A dermoscopic image of a skin lesion:
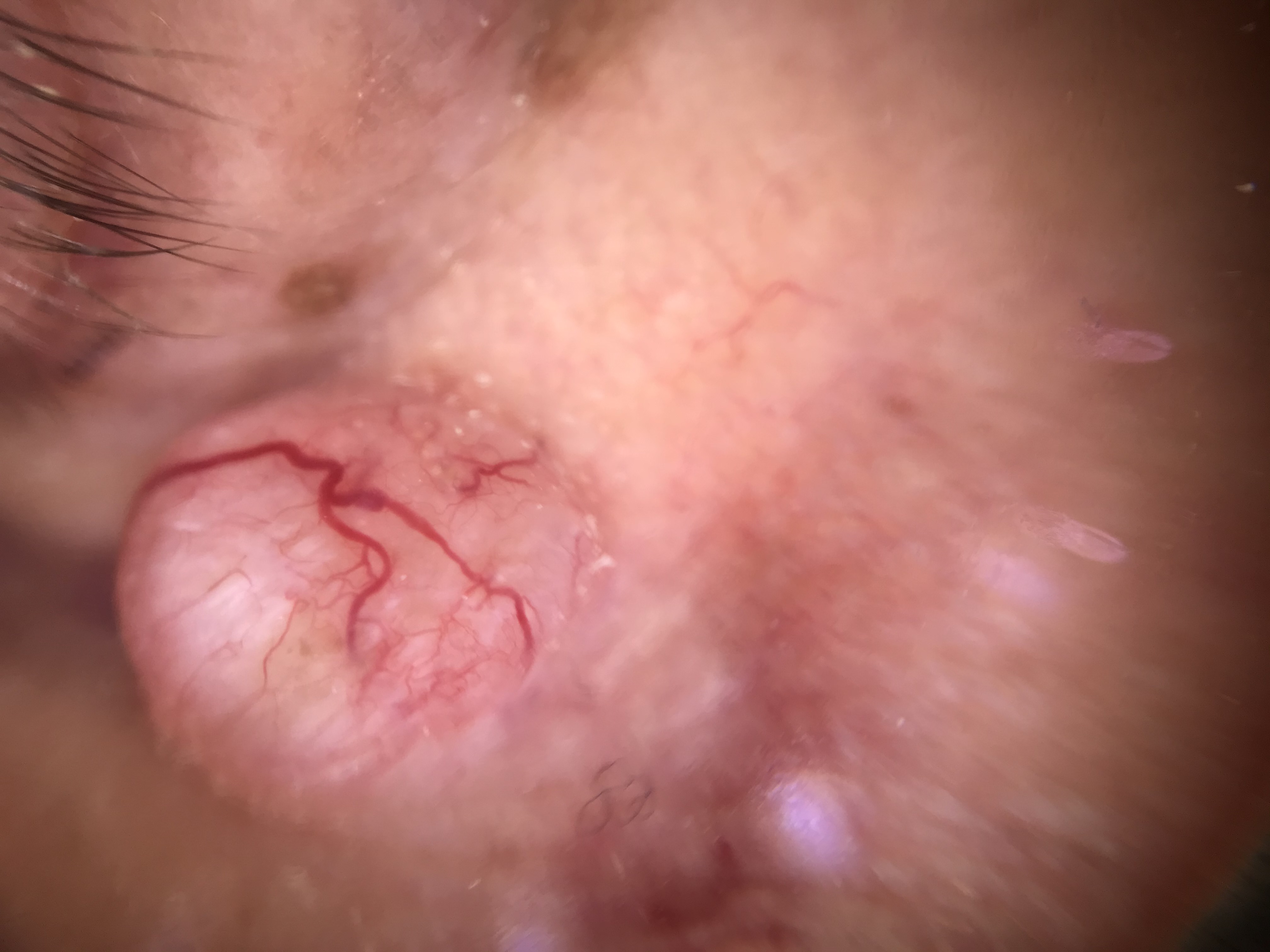classification = keratinocytic; pathology = basal cell carcinoma (biopsy-proven).